A clinical photograph showing a skin lesion; acquired for a research image collection, with no referral diagnosis: 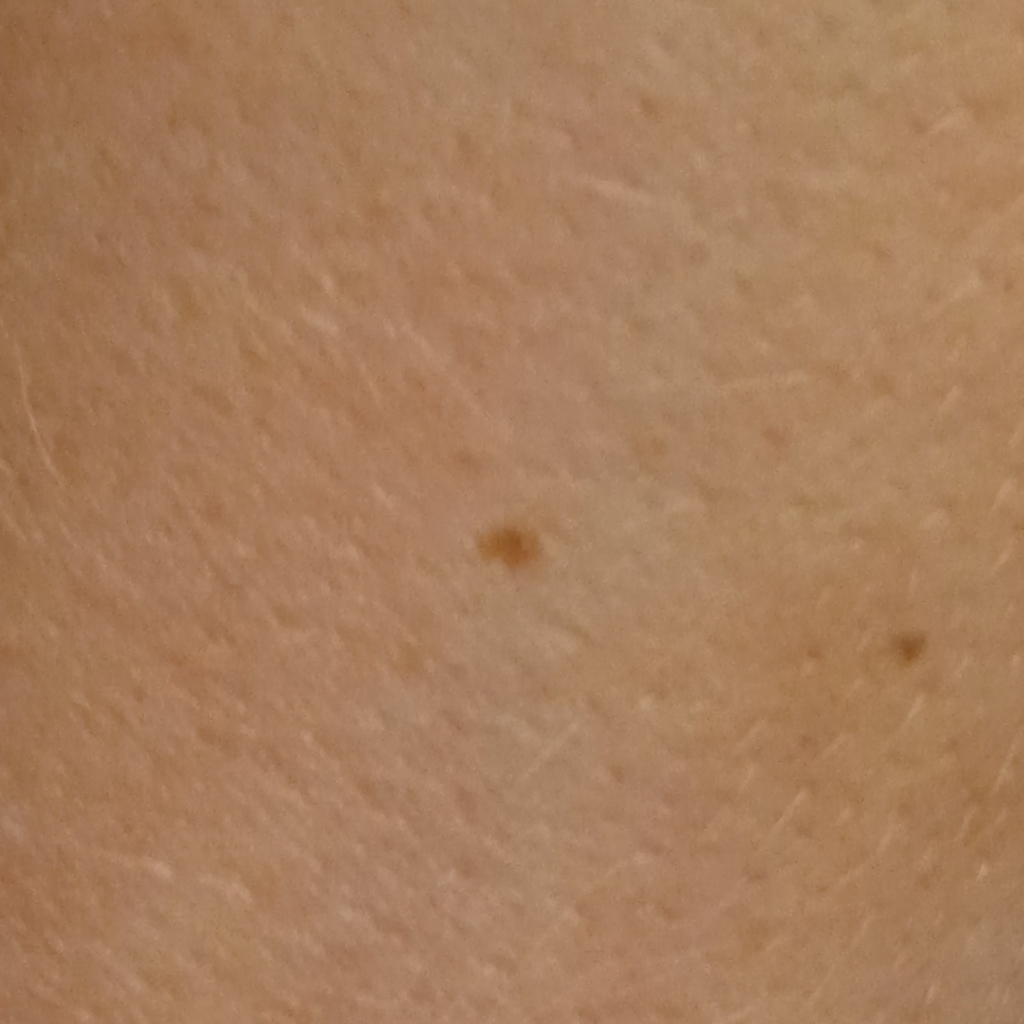The lesion is on an arm. The dermatologists' assessment was a melanocytic nevus.